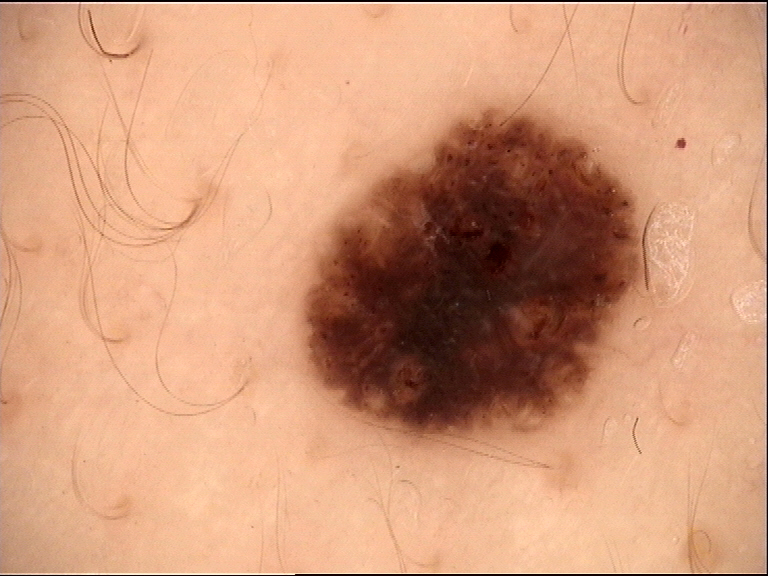diagnosis: dysplastic compound nevus (expert consensus).